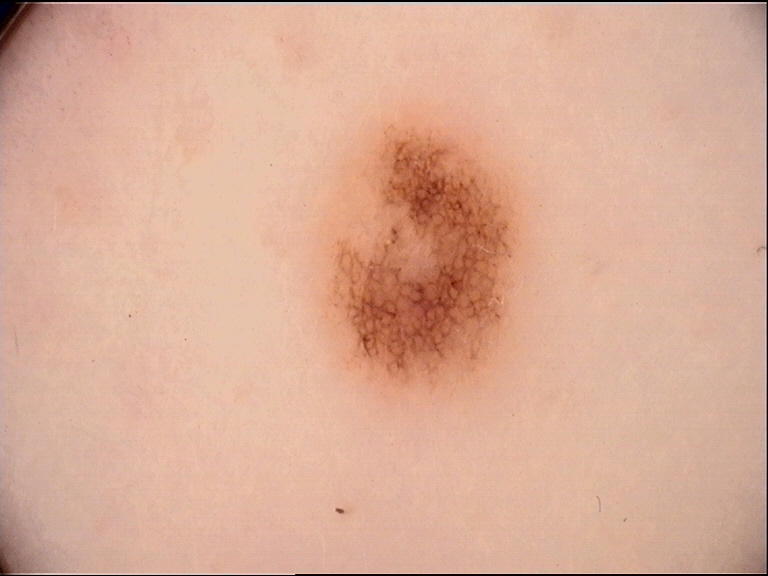Summary: A dermoscopic image of a skin lesion. Conclusion: The diagnosis was a benign lesion — a dysplastic junctional nevus.